A smartphone photograph of a skin lesion. The patient is Fitzpatrick II.
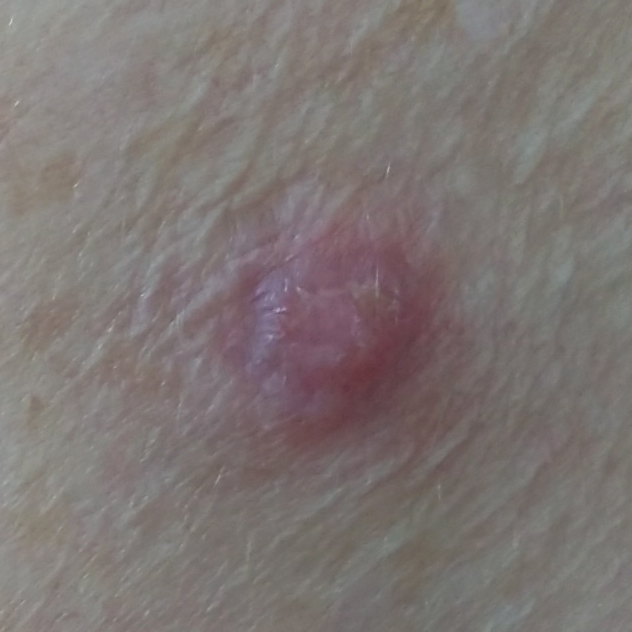Case:
• diameter · 8 × 6 mm
• patient-reported symptoms · elevation, itching
• diagnostic label · squamous cell carcinoma (biopsy-proven)